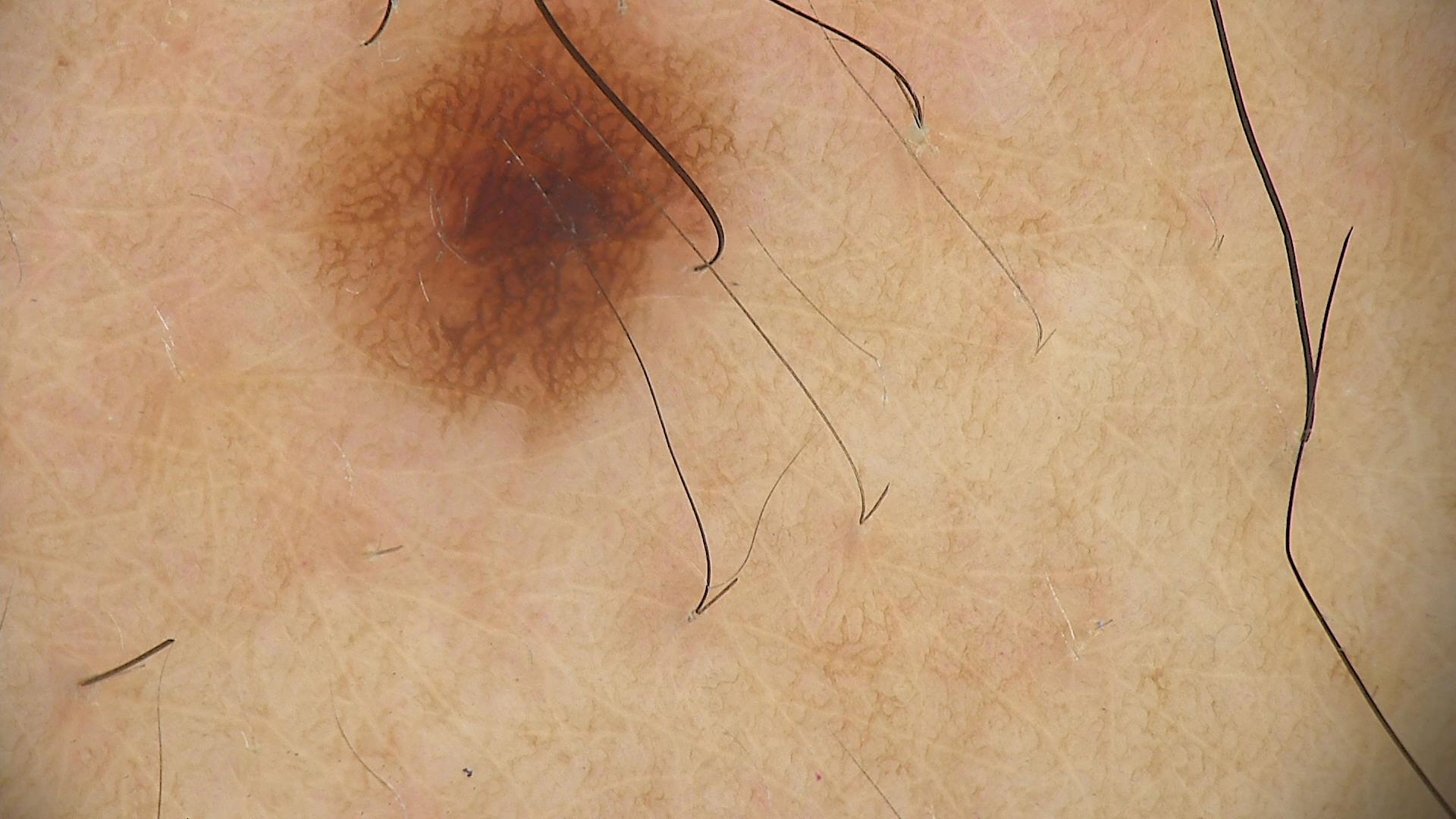assessment — dysplastic junctional nevus (expert consensus).